The patient indicates bleeding, itching, darkening and enlargement · the lesion is described as raised or bumpy and rough or flaky · male patient, age 18–29 · no constitutional symptoms were reported · an image taken at an angle · the patient indicates the condition has been present for one to three months · the arm and leg are involved · the patient described the issue as a rash: 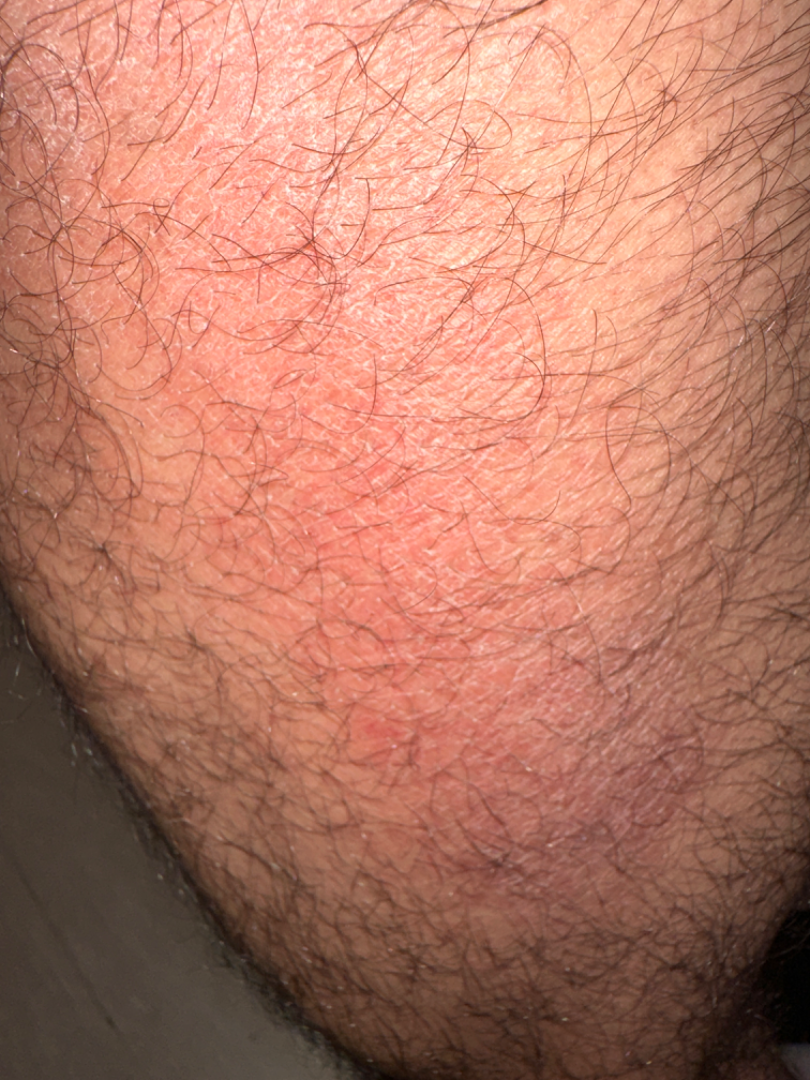Q: What is the dermatologist's impression?
A: favoring Eczema; also consider Irritant Contact Dermatitis